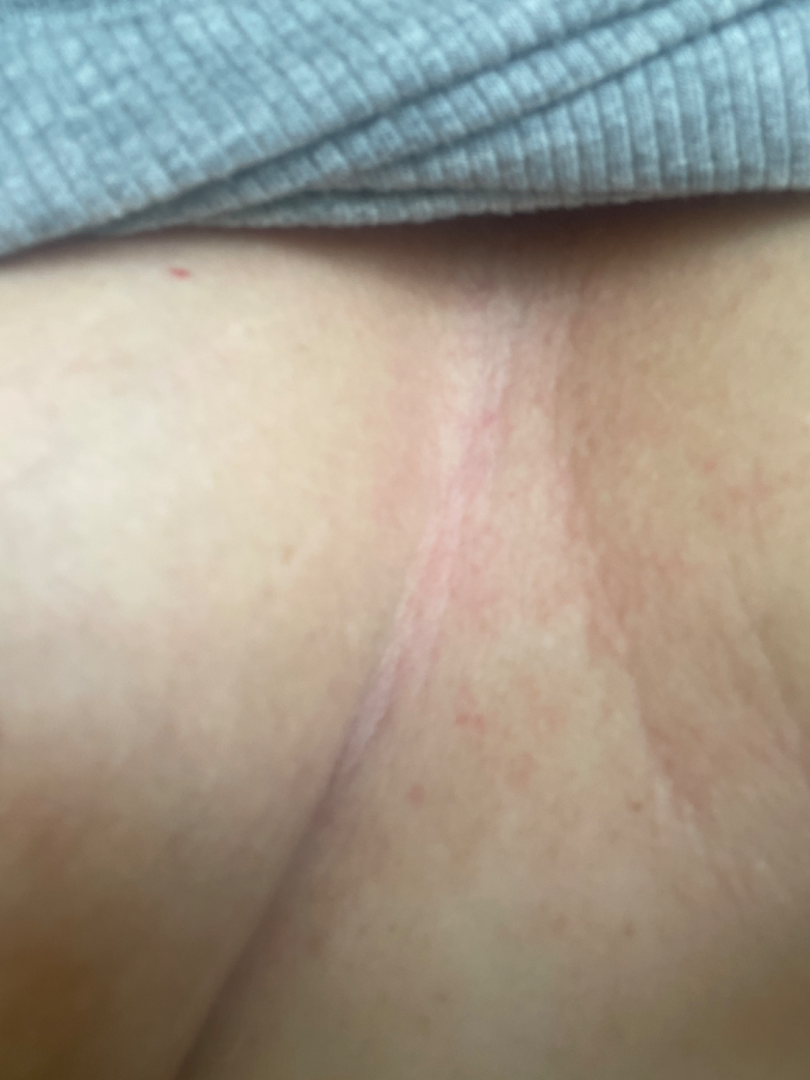The lesion involves the front of the torso. Reported duration is one to three months. Female contributor, age 40–49. The patient indicates the lesion is raised or bumpy. Self-categorized by the patient as a rash. Lay graders estimated a Monk skin tone scale of 3. This is a close-up image. On remote dermatologist review, the differential is split between Tinea Versicolor, Psoriasis and Eczema.